The condition has been present for less than one week · Fitzpatrick phototype II; non-clinician graders estimated 3 on the Monk skin tone scale · the photo was captured at an angle · texture is reported as fluid-filled and raised or bumpy · located on the back of the hand: 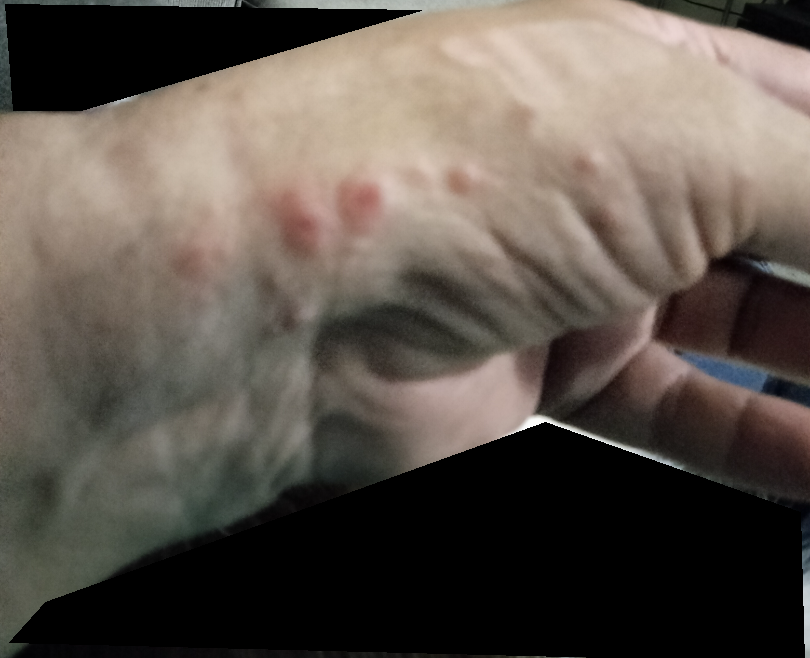dermatologist impression — single-reviewer assessment: most consistent with Insect Bite; also raised was Urticaria; with consideration of Allergic Contact Dermatitis